Skin tone: Fitzpatrick IV; lay reviewers estimated Monk Skin Tone 3 (US pool) or 4 (India pool). This is a close-up image.
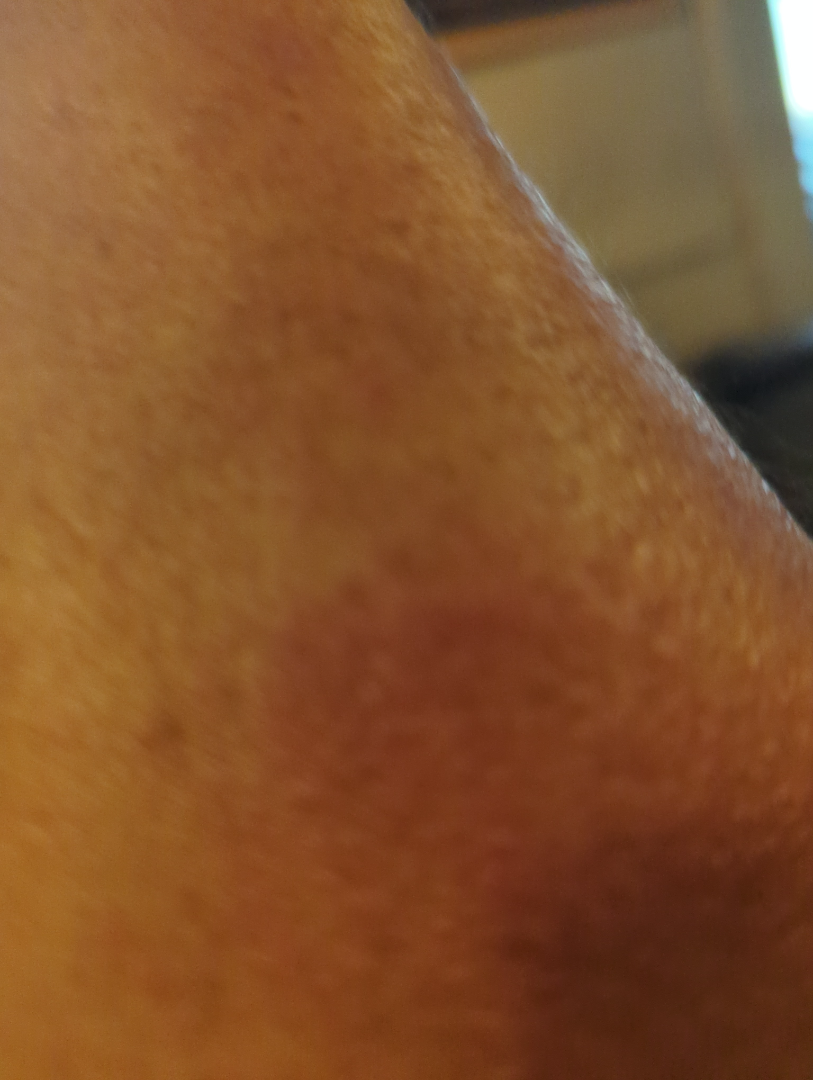| feature | finding |
|---|---|
| assessment | ungradable on photographic review |